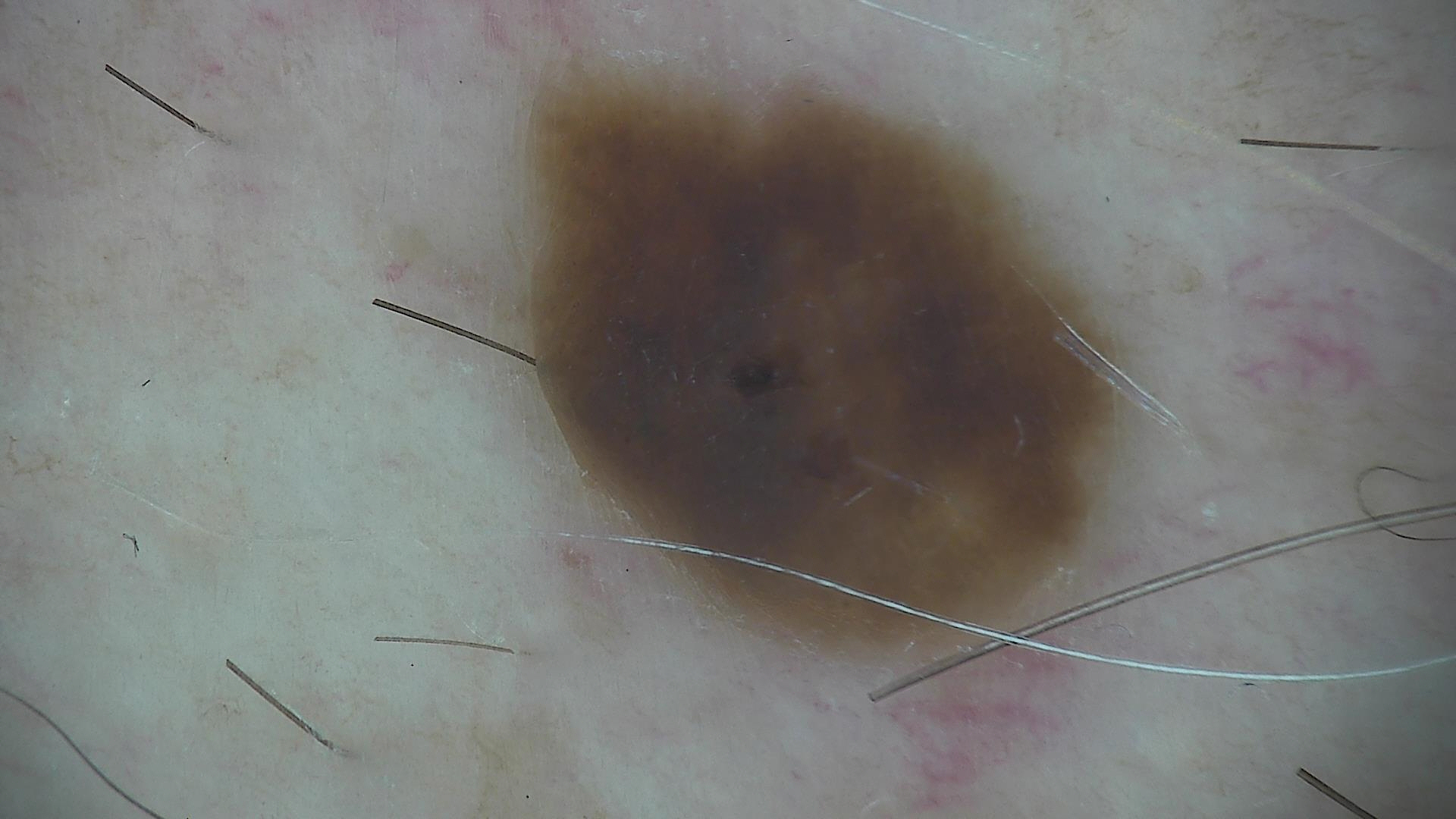lesion type: keratinocytic; diagnosis: seborrheic keratosis (expert consensus).